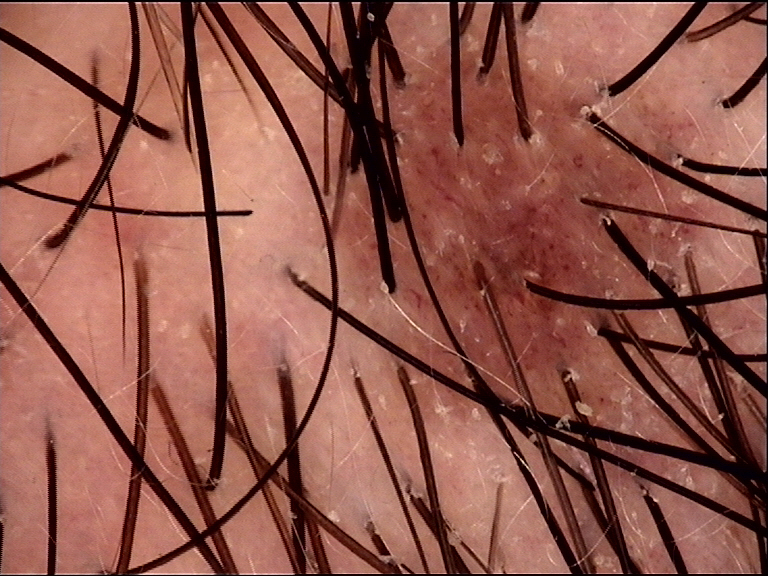A dermoscopic close-up of a skin lesion. Diagnosed as a banal lesion — a compound nevus.